A female subject, roughly 30 years of age. A dermoscopic close-up of a skin lesion: 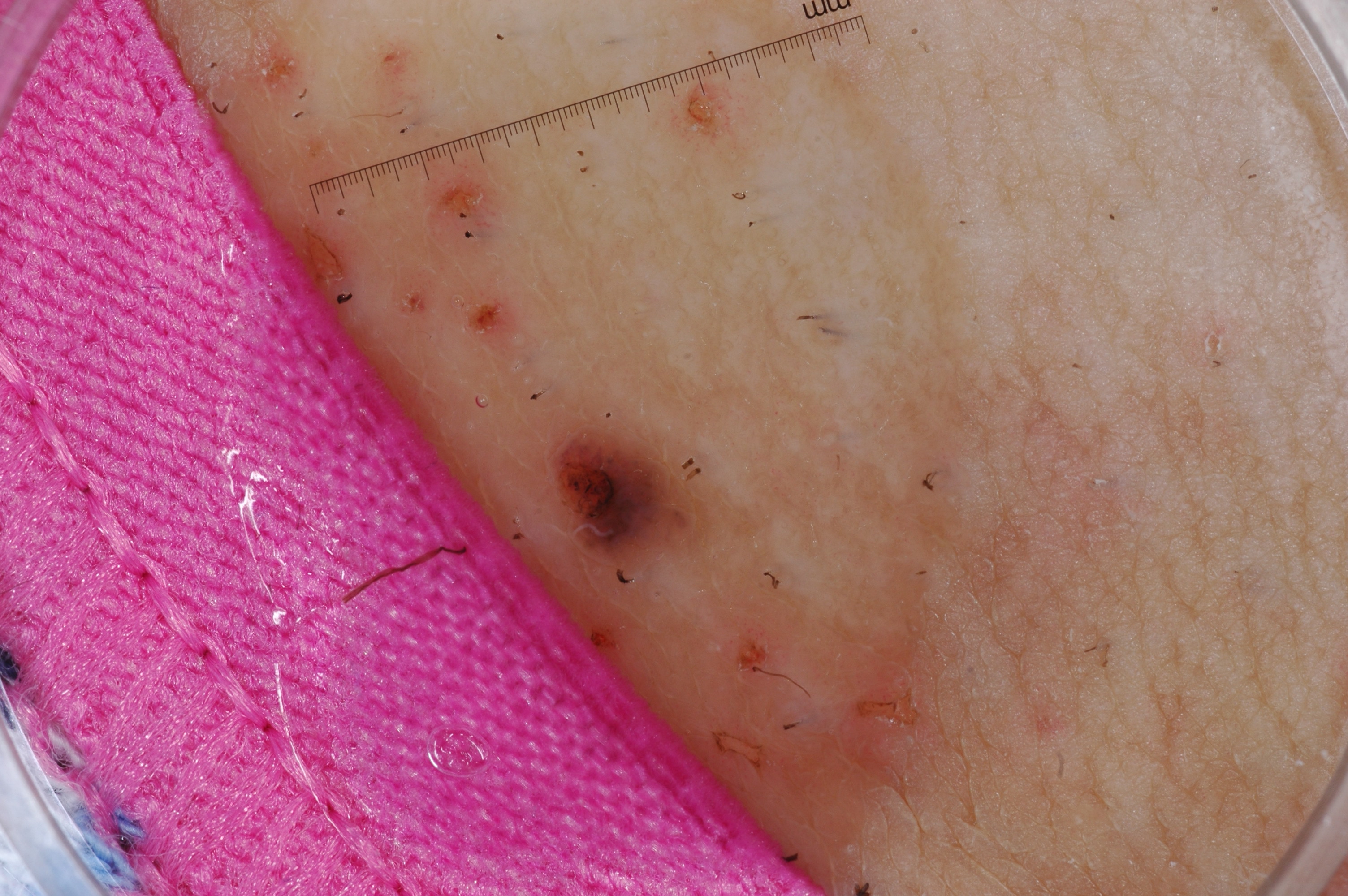location: 543 426 700 577
absent dermoscopic features: pigment network, negative network, milia-like cysts, and streaks
lesion size: ~2% of the field
impression: a melanocytic nevus